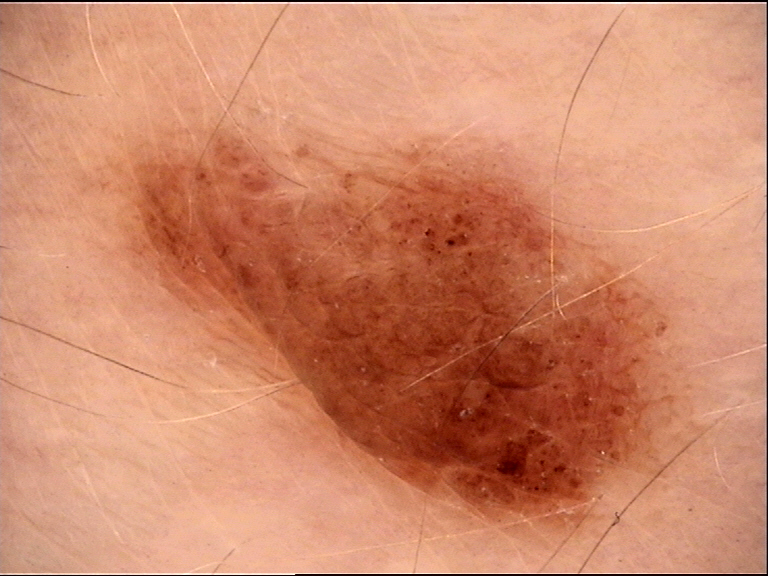Q: What was the diagnostic impression?
A: compound nevus (expert consensus)